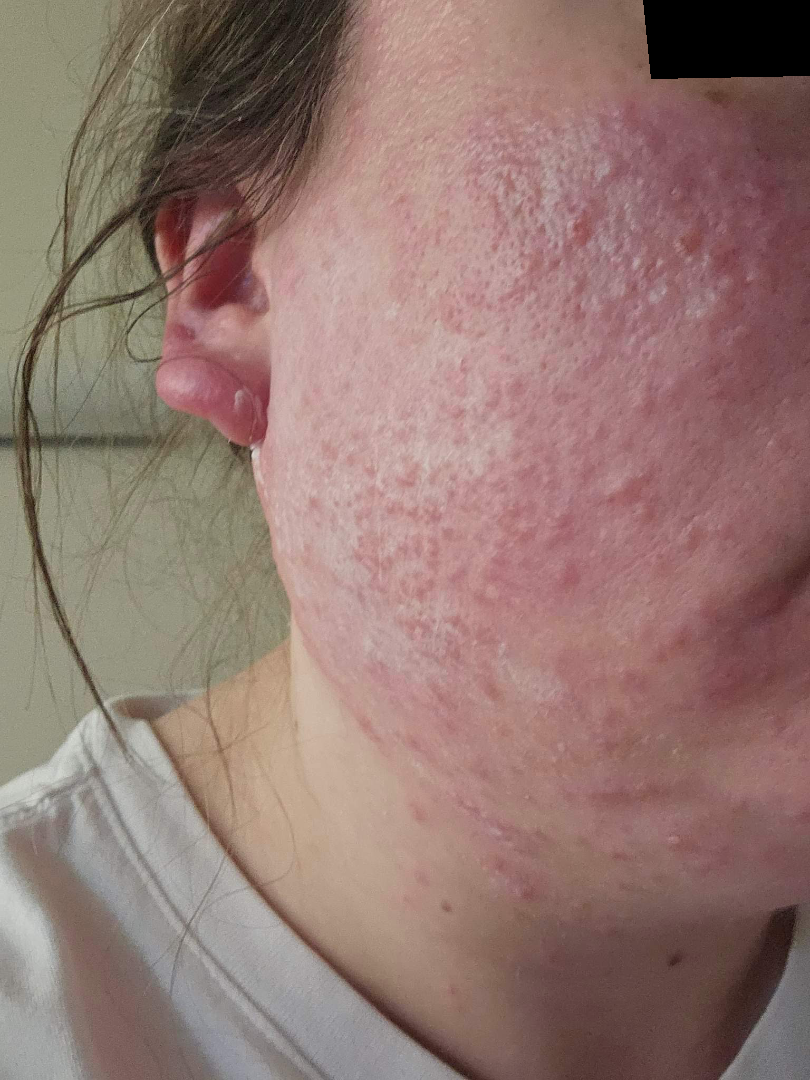Patient information:
This is a close-up image.
Review:
The reviewing clinician's impression was: favoring Rosacea; also raised was Acne.